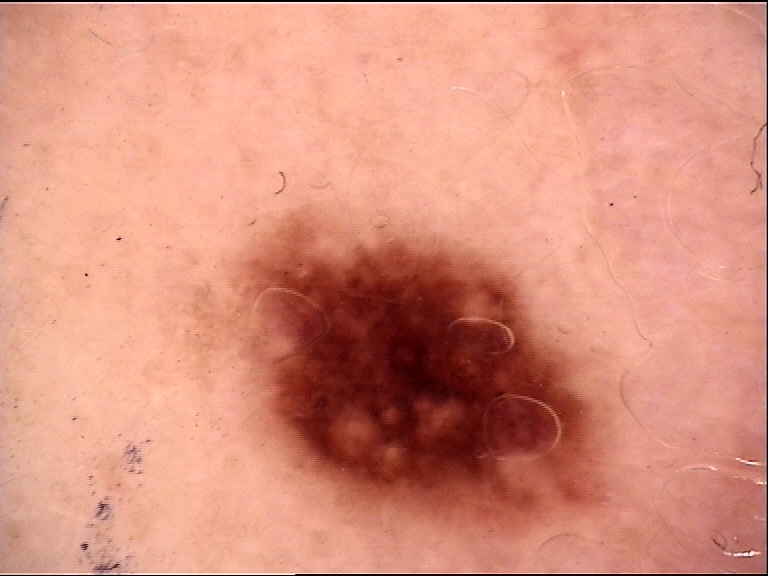Q: What is the imaging modality?
A: dermoscopy
Q: What is this lesion?
A: dysplastic junctional nevus (expert consensus)